The patient described the issue as a rash; no constitutional symptoms were reported; reported duration is more than five years; close-up view; the sole of the foot is involved.
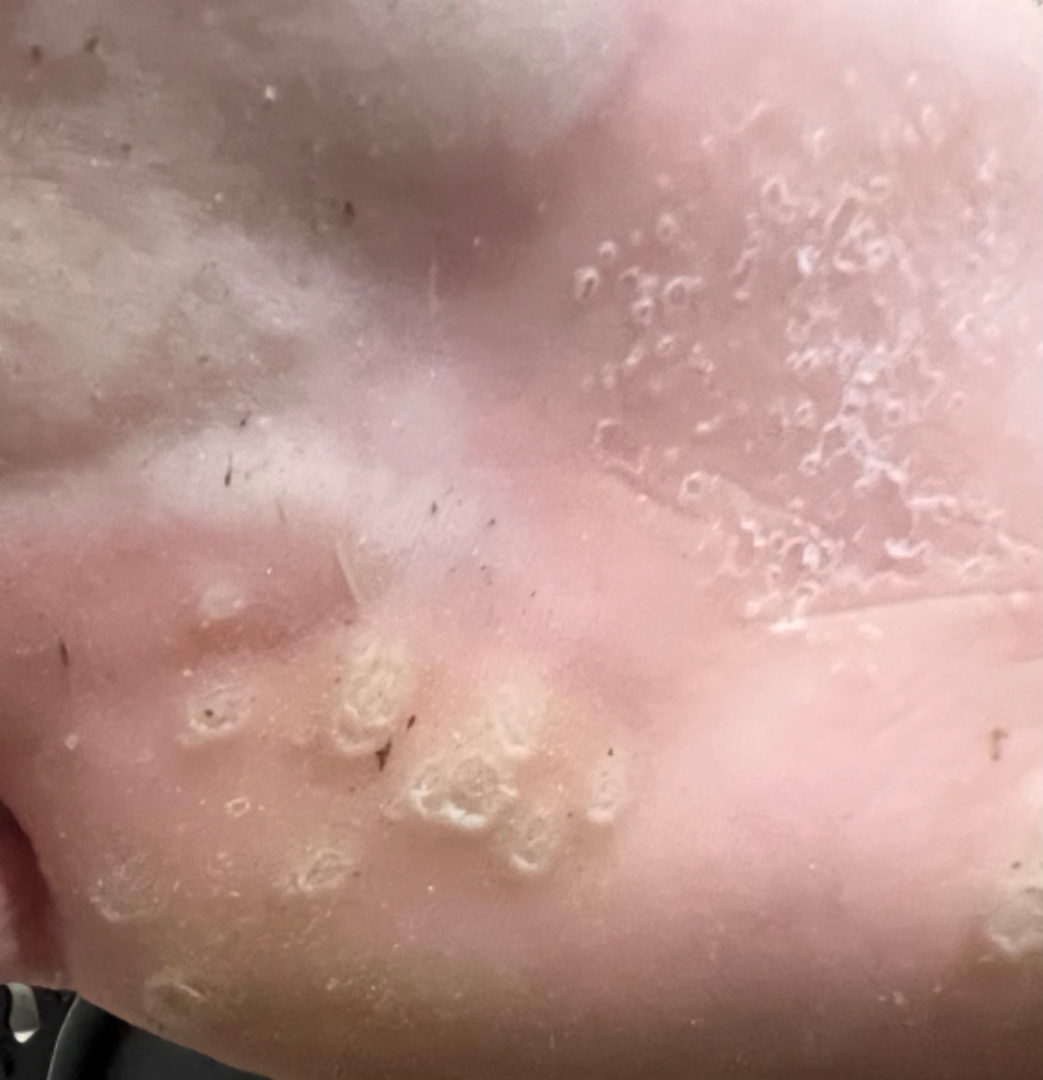| feature | finding |
|---|---|
| clinical impression | Verruca vulgaris (favored) |